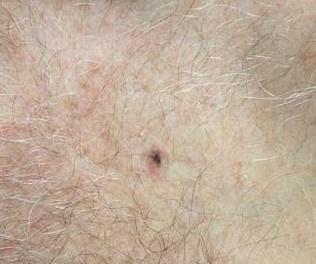A male subject aged approximately 75.
The chart notes a prior melanoma.
A clinical overview photograph of a skin lesion.
Fitzpatrick skin type II.
The lesion was found on the trunk (the anterior trunk).
Histopathologically confirmed as a melanoma.